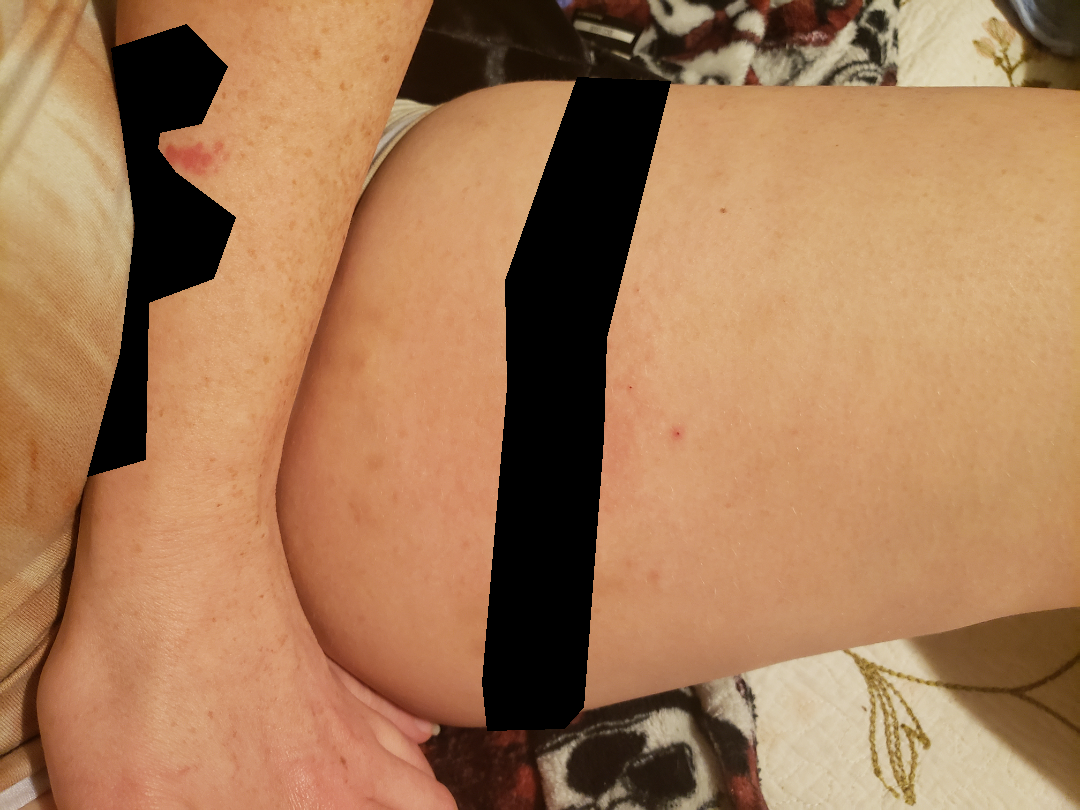Self-categorized by the patient as a rash.
The photo was captured at a distance.
The lesion is associated with itching and bothersome appearance.
The leg is involved.
The lesion is described as raised or bumpy and flat.
Female subject, age 30–39.
The patient indicates the condition has been present for one to four weeks.
Reviewed remotely by three dermatologists: most likely Allergic Contact Dermatitis; also consider Folliculitis; lower on the differential is Urticaria; a more distant consideration is Eczema.